Close-up view · located on the arm, back of the torso and leg.
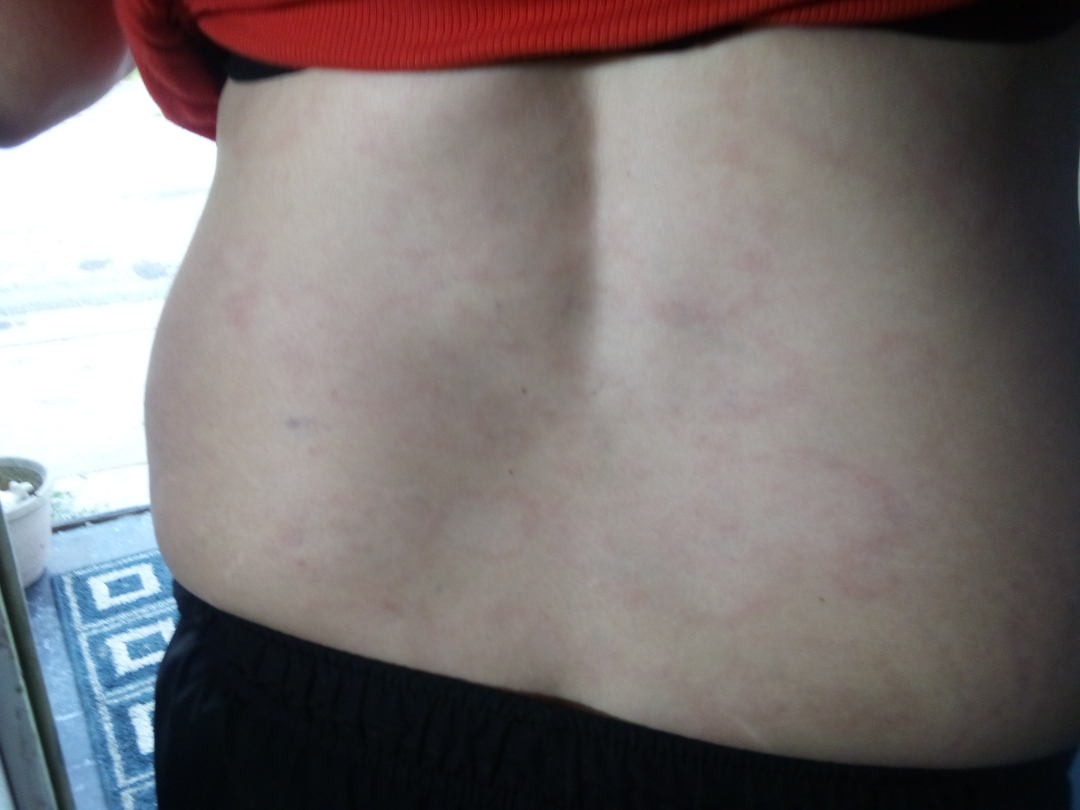| feature | finding |
|---|---|
| duration | three to twelve months |
| skin tone | Fitzpatrick phototype IV; human graders estimated 2 on the Monk skin tone scale |
| diagnostic considerations | most consistent with Urticaria; possibly Annular erythema; also on the differential is Leukocytoclastic Vasculitis |